A female patient aged approximately 35 · a skin lesion imaged with a dermatoscope · the chart records no melanoma in first-degree relatives and no prior melanoma · recorded as Fitzpatrick II:
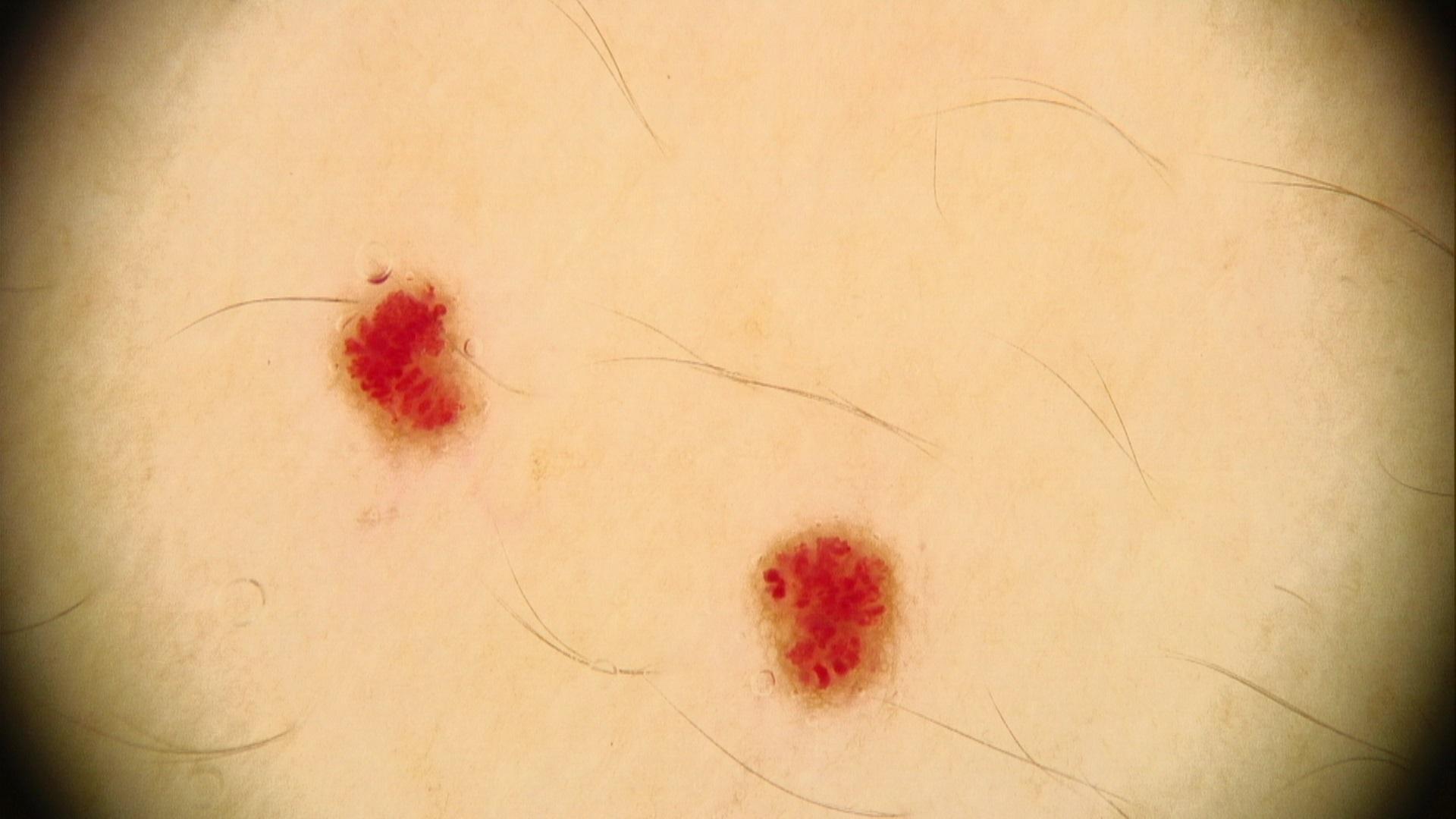body site — the anterior trunk; assessment — vascular lesion.